The contributor reports the condition has been present for one to four weeks, no relevant lesion symptoms reported, texture is reported as raised or bumpy, the subject is a female aged 18–29, the photo was captured at an angle, self-categorized by the patient as a rash: 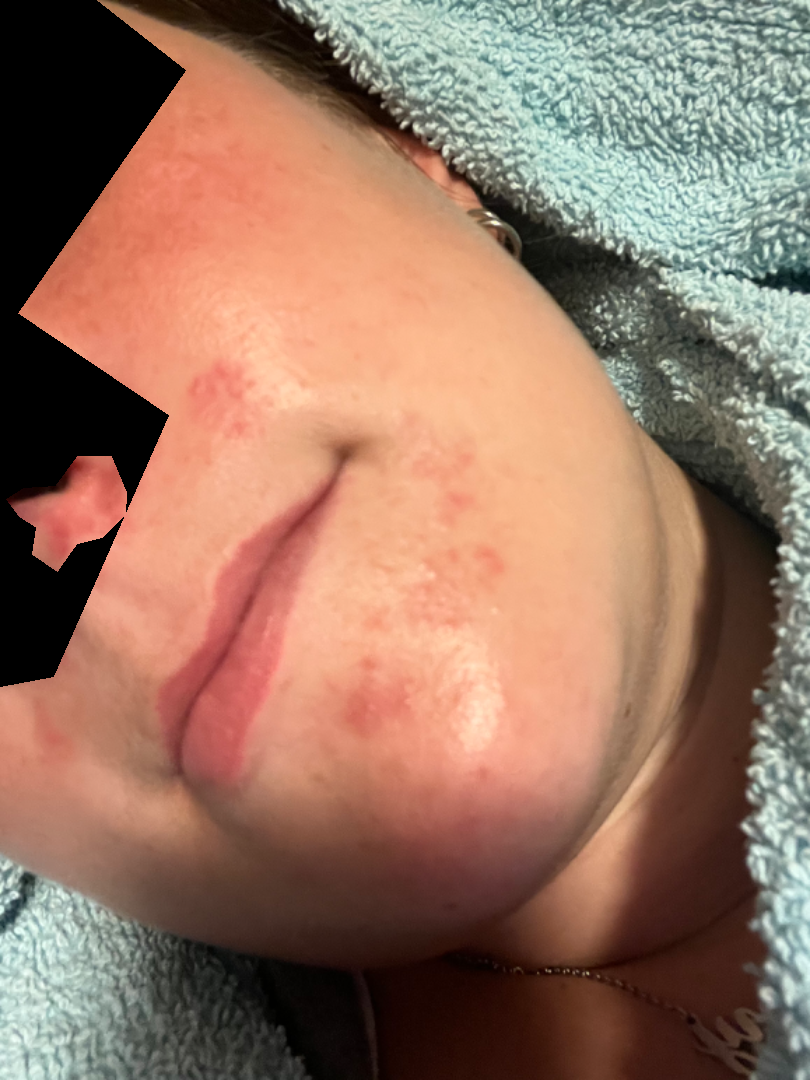differential diagnosis = reviewed remotely by one dermatologist: in keeping with Perioral Dermatitis.